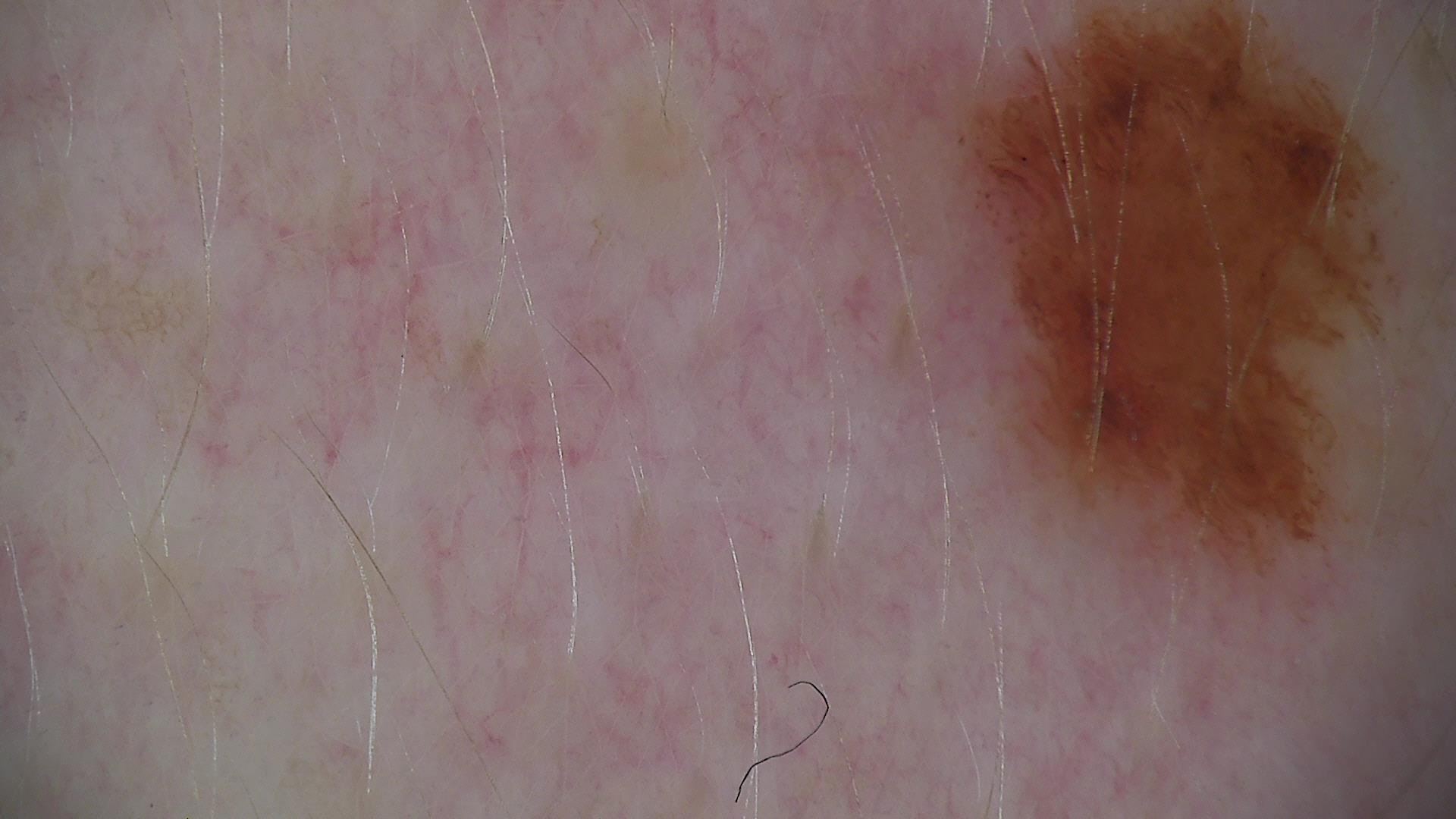Dermoscopy of a skin lesion.
The diagnostic label was a benign lesion — a dysplastic junctional nevus.